Close-up view; the subject is a male aged 18–29; the head or neck is involved: 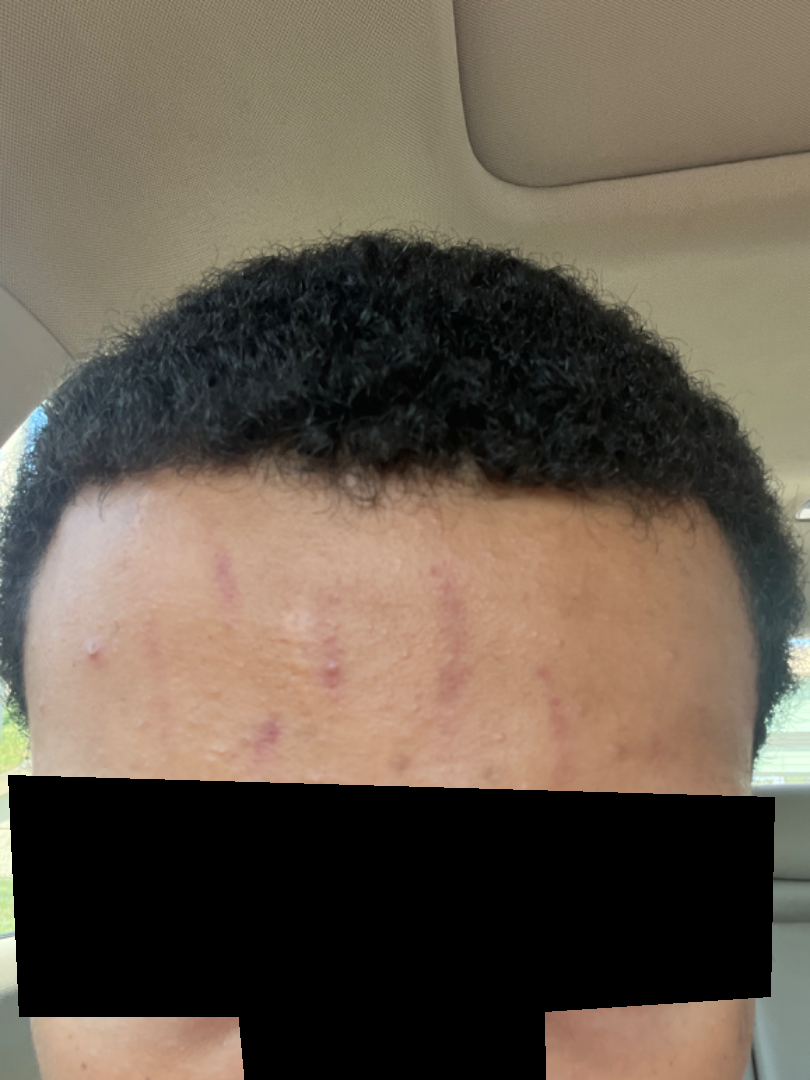history — about one day | self-categorized as — a rash | surface texture — flat | skin tone — lay graders estimated Monk skin tone scale 3 or 5 (two reviewer pools disagreed) | lesion symptoms — none reported | assessment — the differential, in no particular order, includes Scar Condition, Lichen planus/lichenoid eruption and Post-Inflammatory hyperpigmentation.